A dermatoscopic image of a skin lesion.
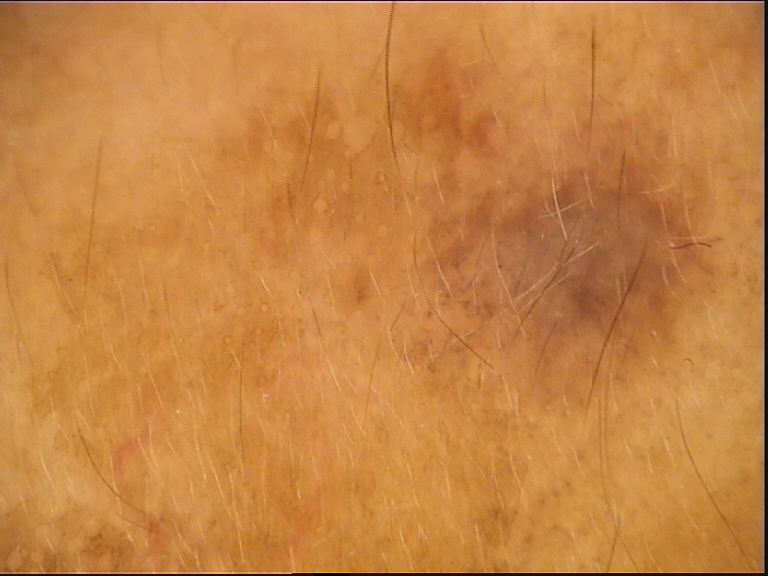Labeled as a dysplastic compound nevus.